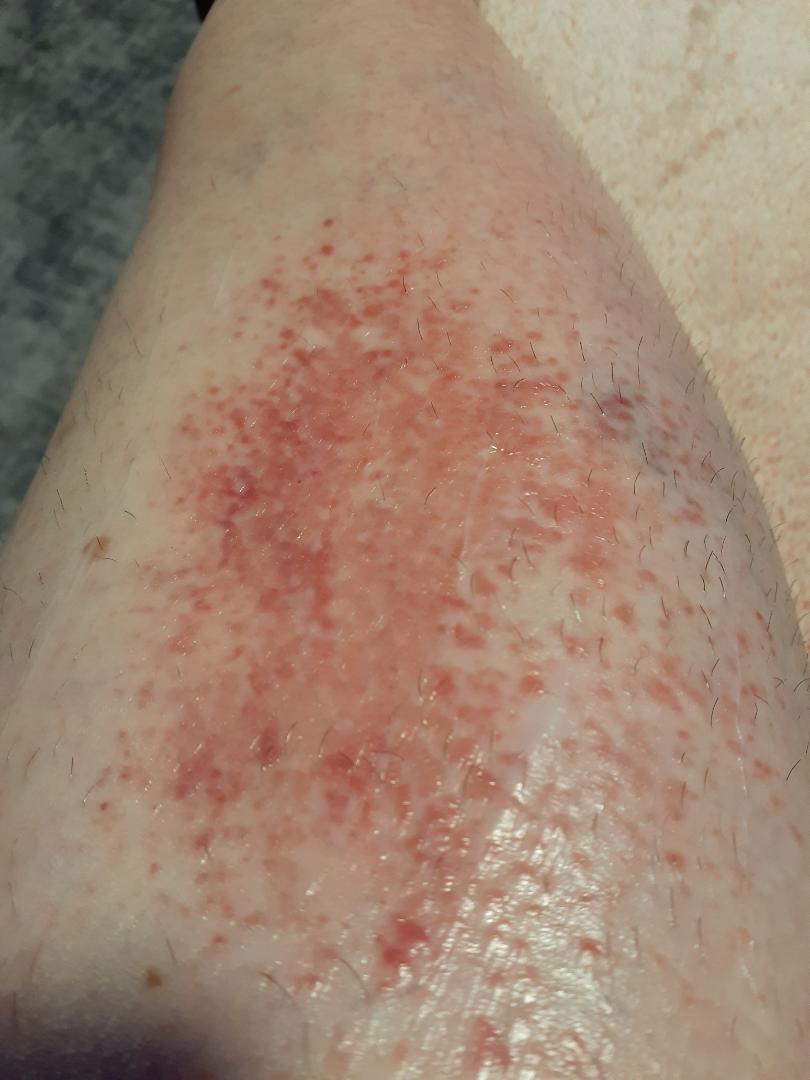The lesion is described as raised or bumpy. The patient is 50–59, female. Close-up view. The patient indicates bothersome appearance, itching and enlargement. Self-categorized by the patient as a rash. The lesion involves the leg. No associated systemic symptoms reported. On teledermatology review: the differential, in no particular order, includes Acute dermatitis, NOS and Stasis Dermatitis; less likely is Eczema; less probable is Burn of skin; a remote consideration is Allergic Contact Dermatitis; lower on the differential is Amyloidosis of skin.